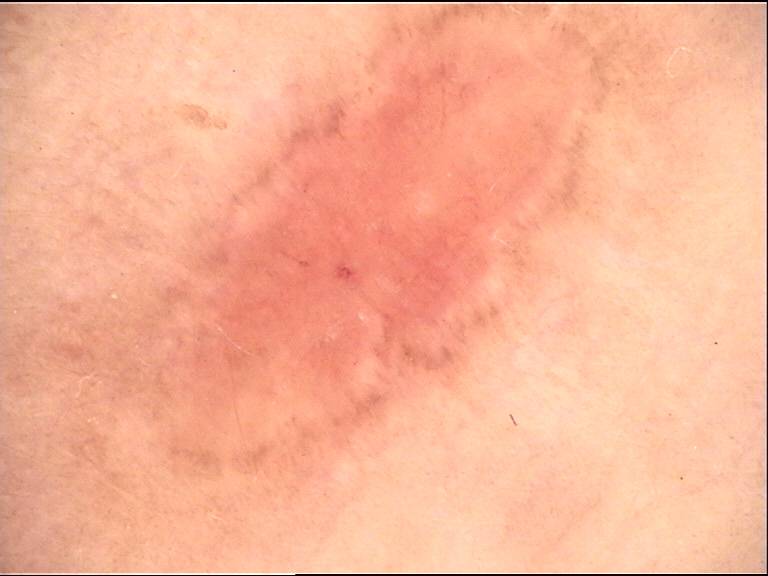The biopsy diagnosis was a keratinocytic, malignant lesion — a basal cell carcinoma.